A dermoscopy image of a single skin lesion.
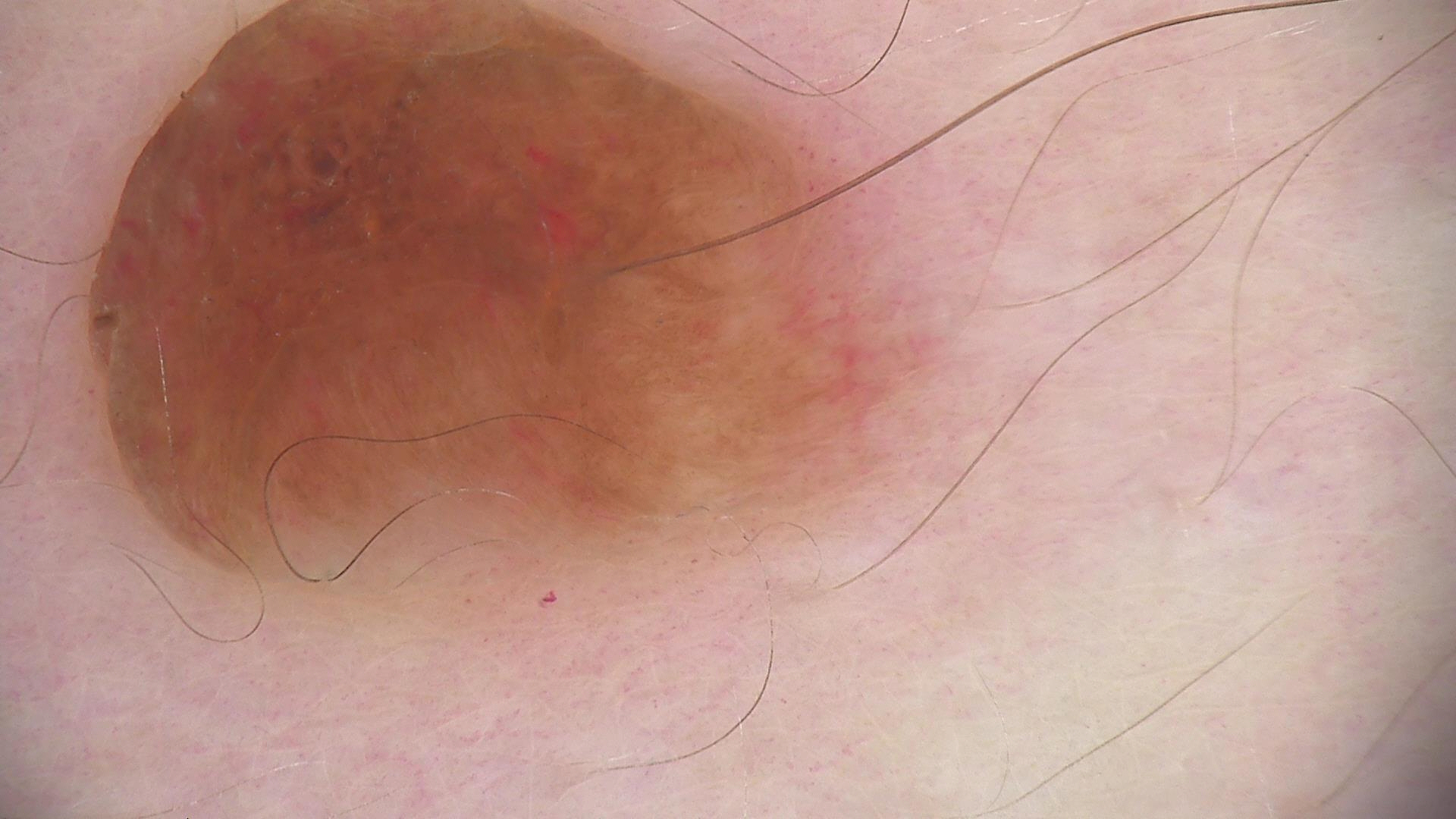Summary: The architecture is that of a banal lesion. Conclusion: The diagnostic label was a dermal nevus.